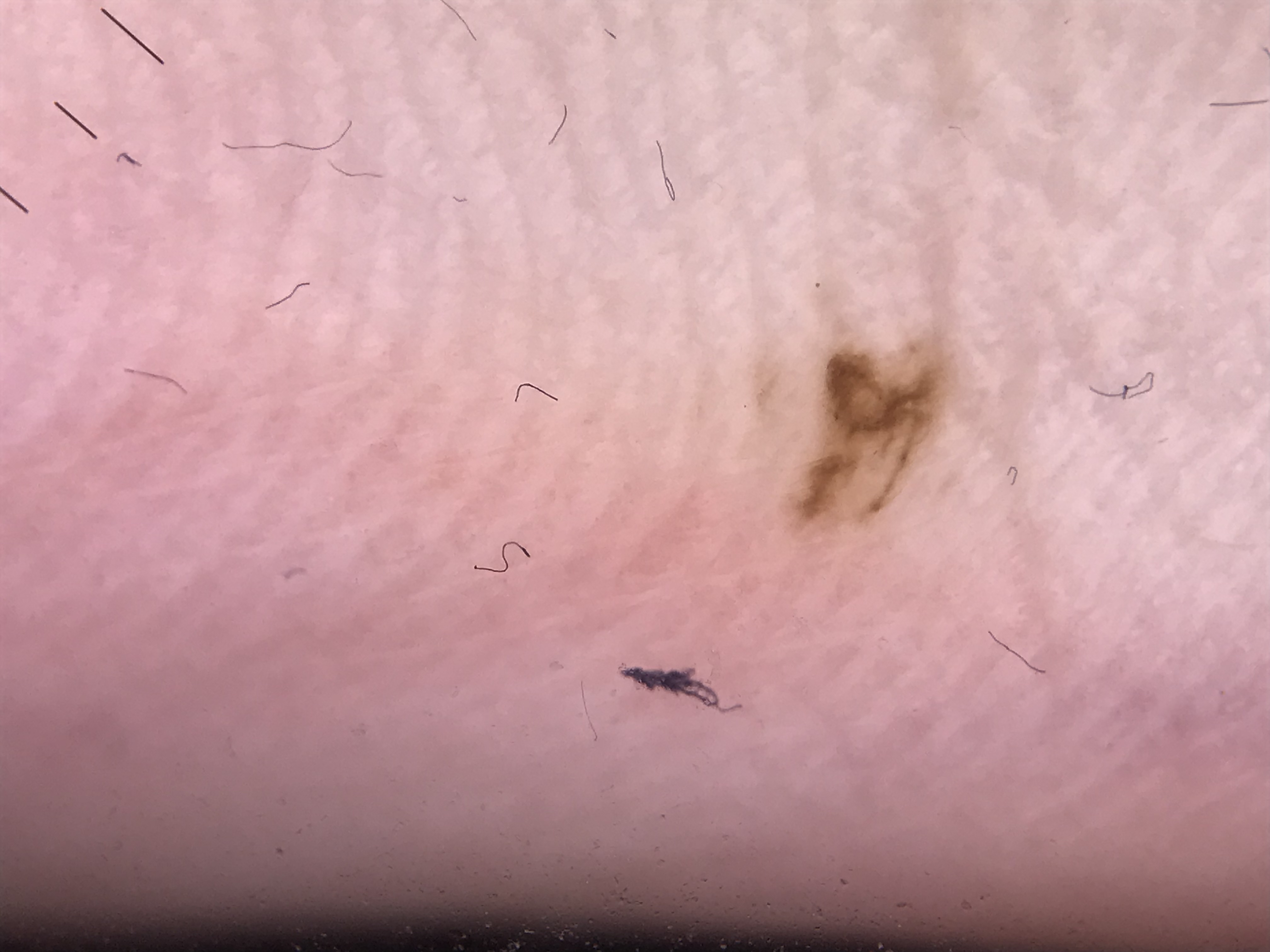Findings:
– category: banal
– diagnostic label: acral junctional nevus (expert consensus)